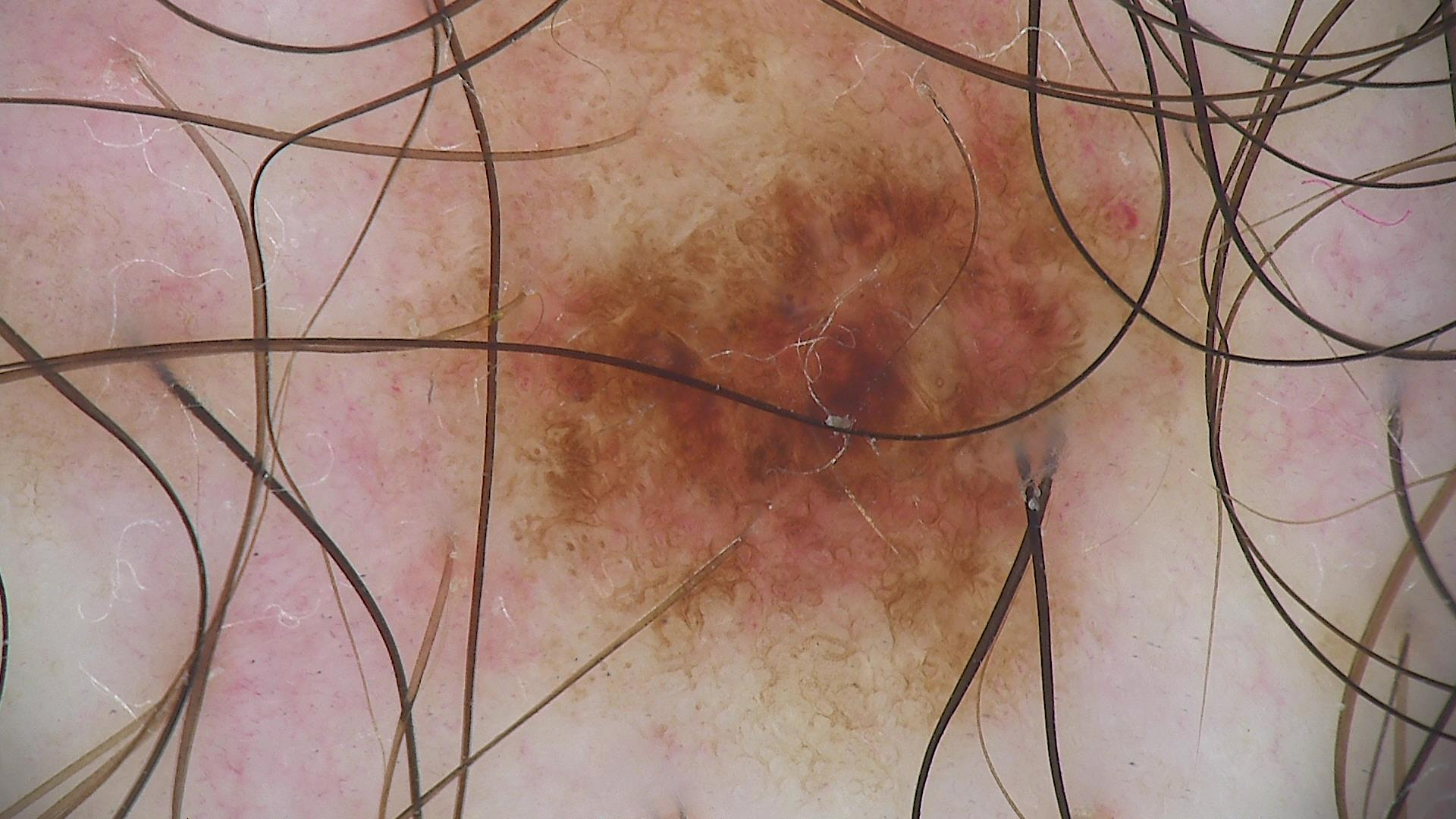<lesion>
  <image>dermatoscopy</image>
  <diagnosis>
    <name>dysplastic compound nevus</name>
    <code>cd</code>
    <malignancy>benign</malignancy>
    <super_class>melanocytic</super_class>
    <confirmation>expert consensus</confirmation>
  </diagnosis>
</lesion>